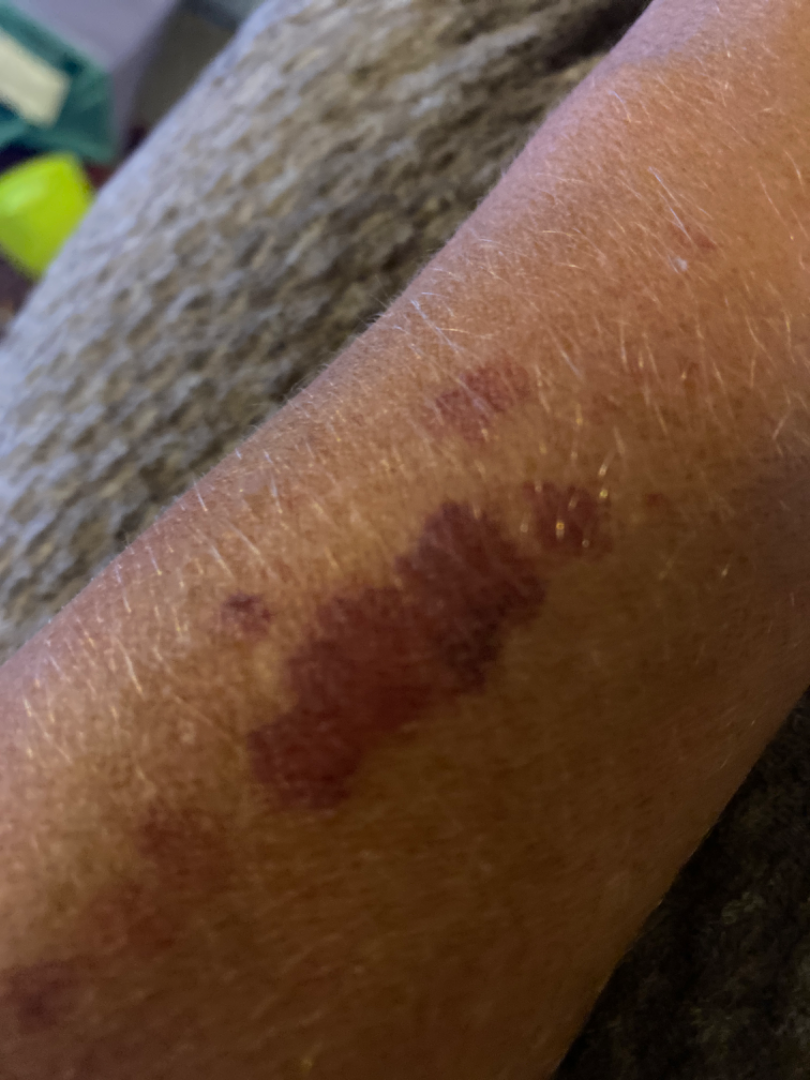Q: What is the dermatologist's impression?
A: one reviewing dermatologist: consistent with ecchymoses